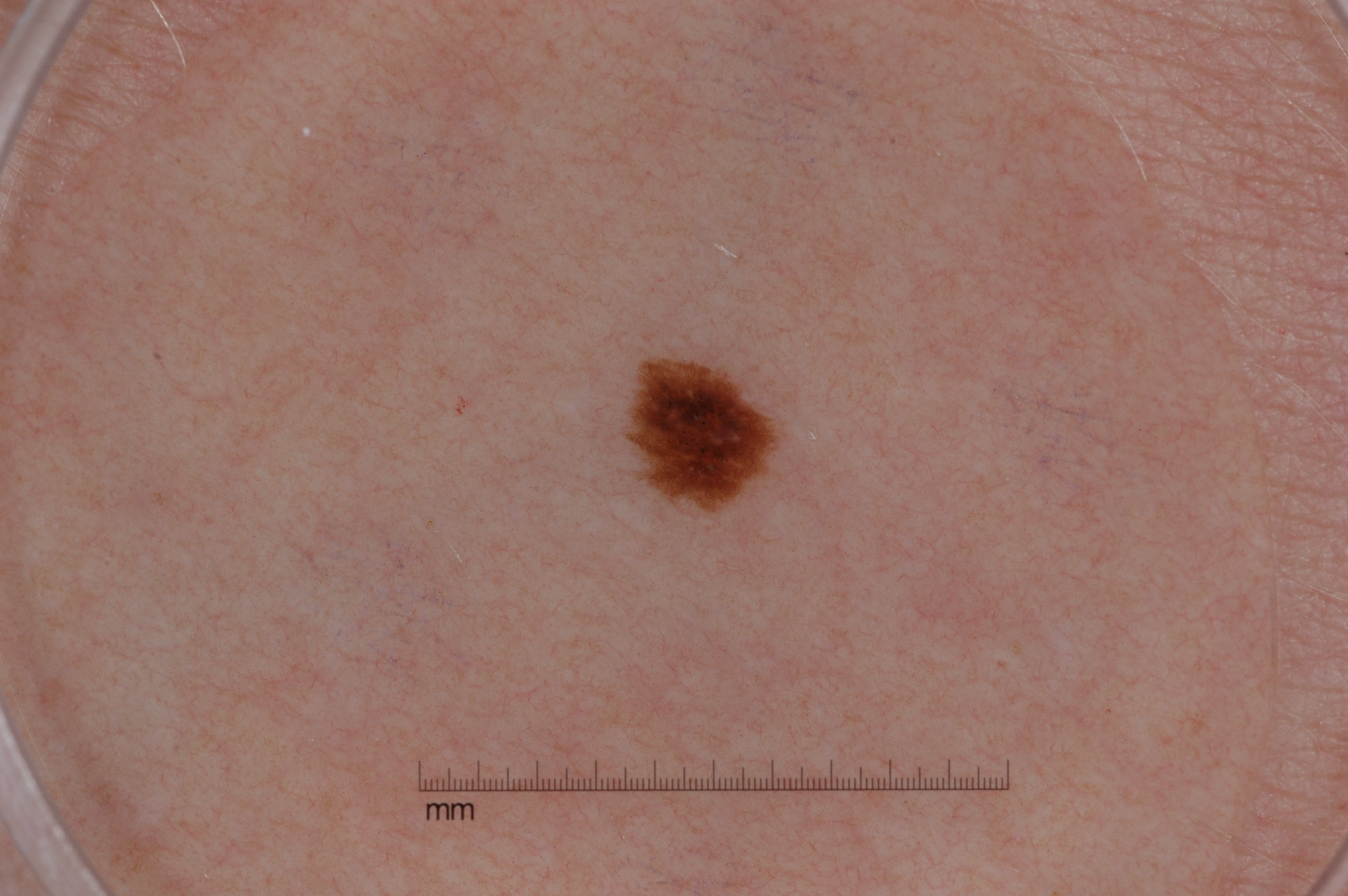The subject is a female roughly 25 years of age.
A dermoscopic view of a skin lesion.
In (x1, y1, x2, y2) order, the lesion occupies the region [618,345,788,519].
Dermoscopic assessment notes pigment network, with no milia-like cysts, negative network, or streaks.
The diagnostic assessment was a melanocytic nevus.